Male patient, age 50–59. A close-up photograph — 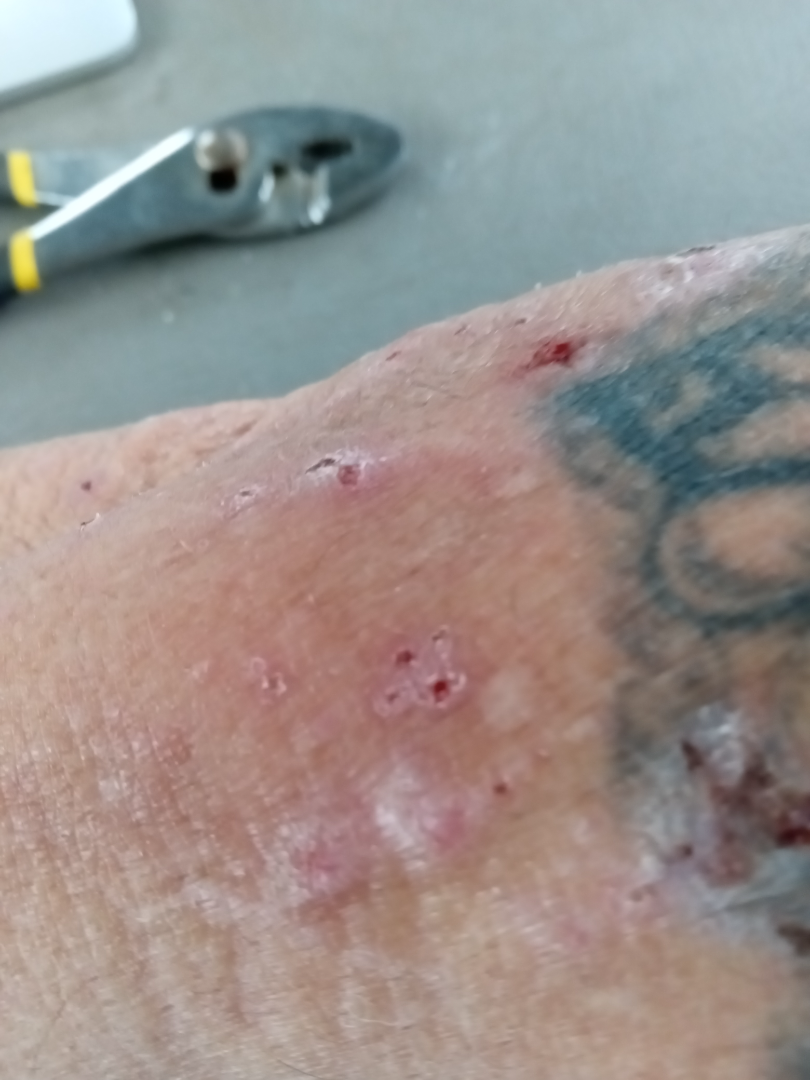Q: Fitzpatrick or Monk tone?
A: self-reported Fitzpatrick IV
Q: What is the dermatologist's impression?
A: in keeping with Lichen Simplex Chronicus